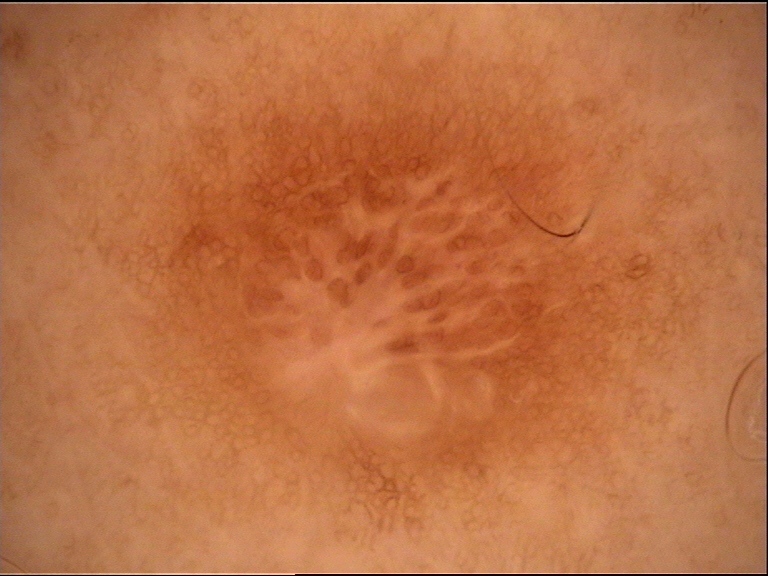Summary:
A dermoscopic photograph of a skin lesion. This is a fibro-histiocytic lesion.
Conclusion:
Diagnosed as a dermatofibroma.